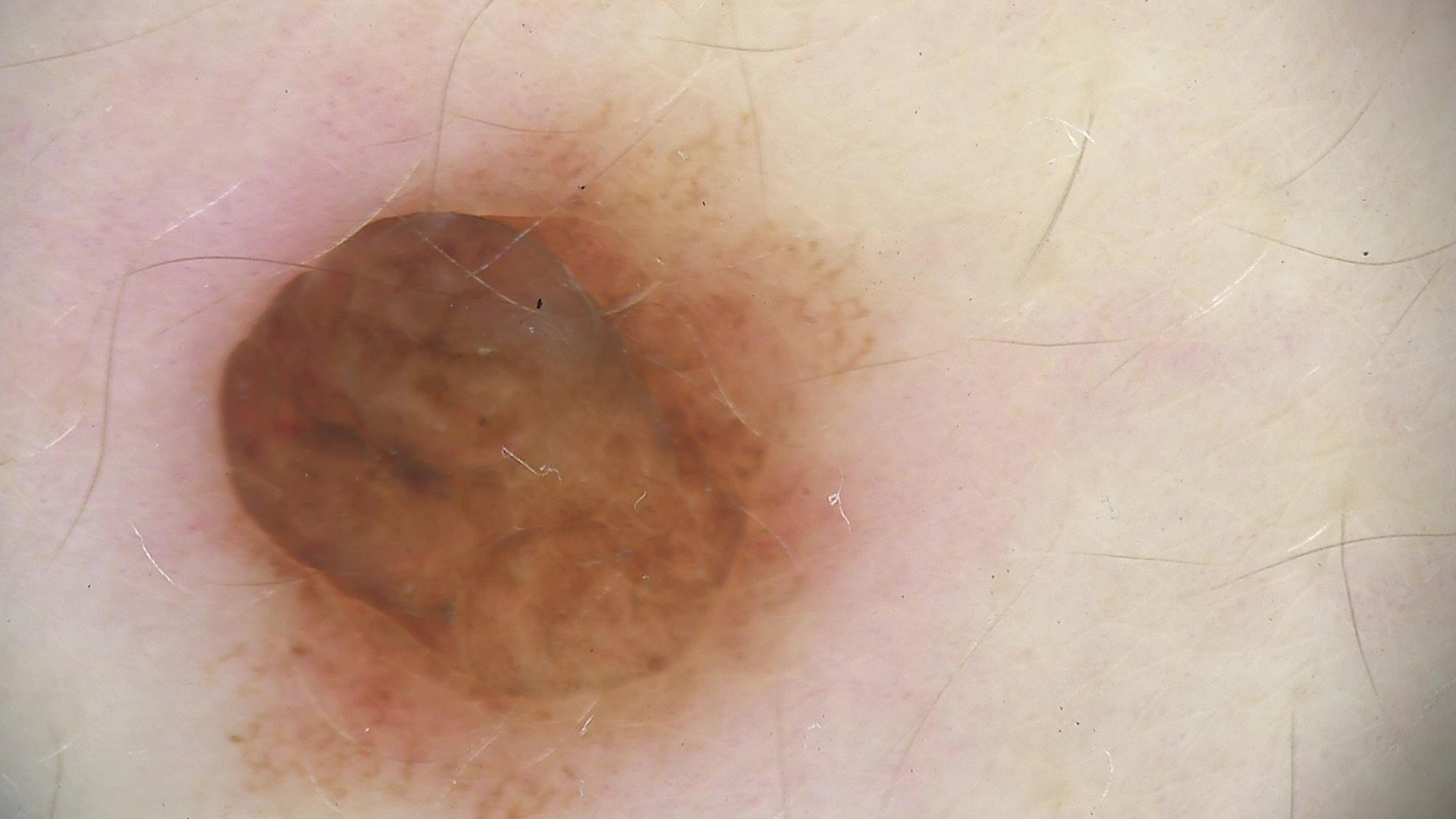Labeled as a dermal nevus.